A skin lesion imaged with a dermatoscope: 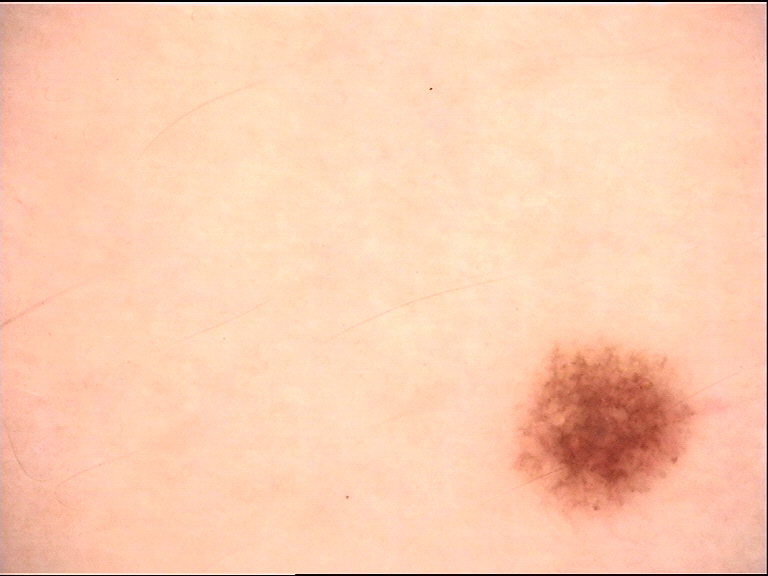Q: What is this lesion?
A: dysplastic junctional nevus (expert consensus)